A dermoscopic image of a skin lesion.
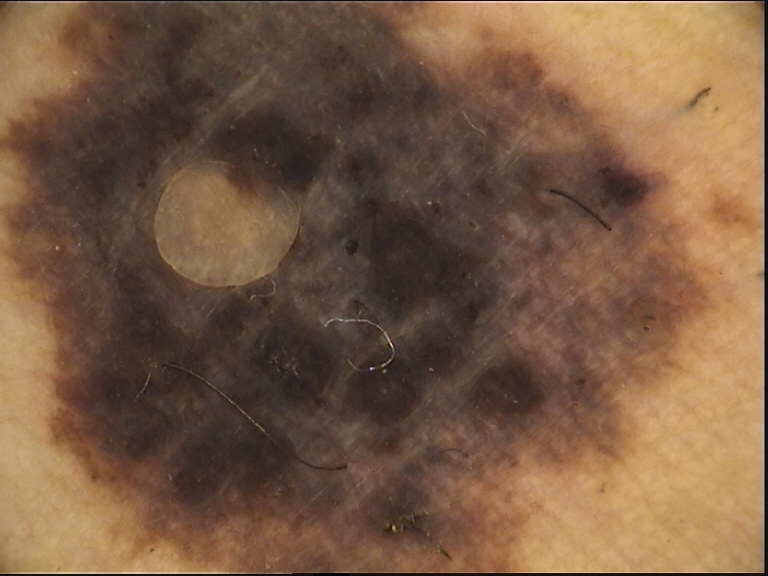The morphology is that of a banal lesion. Diagnosed as a congenital compound nevus.